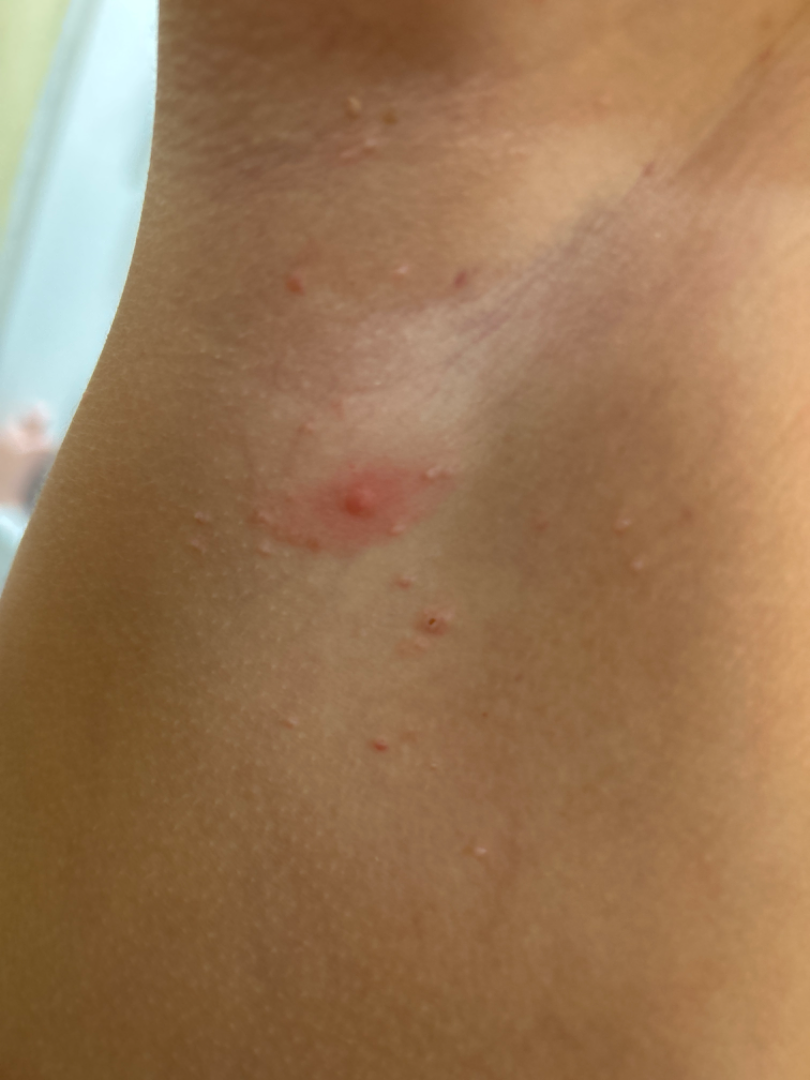Review:
On photographic review by a dermatologist, consistent with Molluscum Contagiosum.